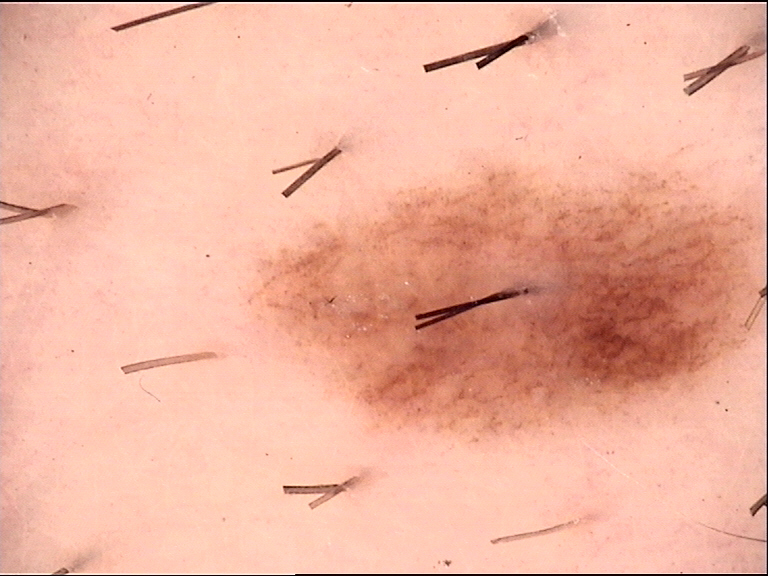Case: A dermoscopy image of a single skin lesion. Impression: The diagnosis was a benign lesion — a dysplastic compound nevus.